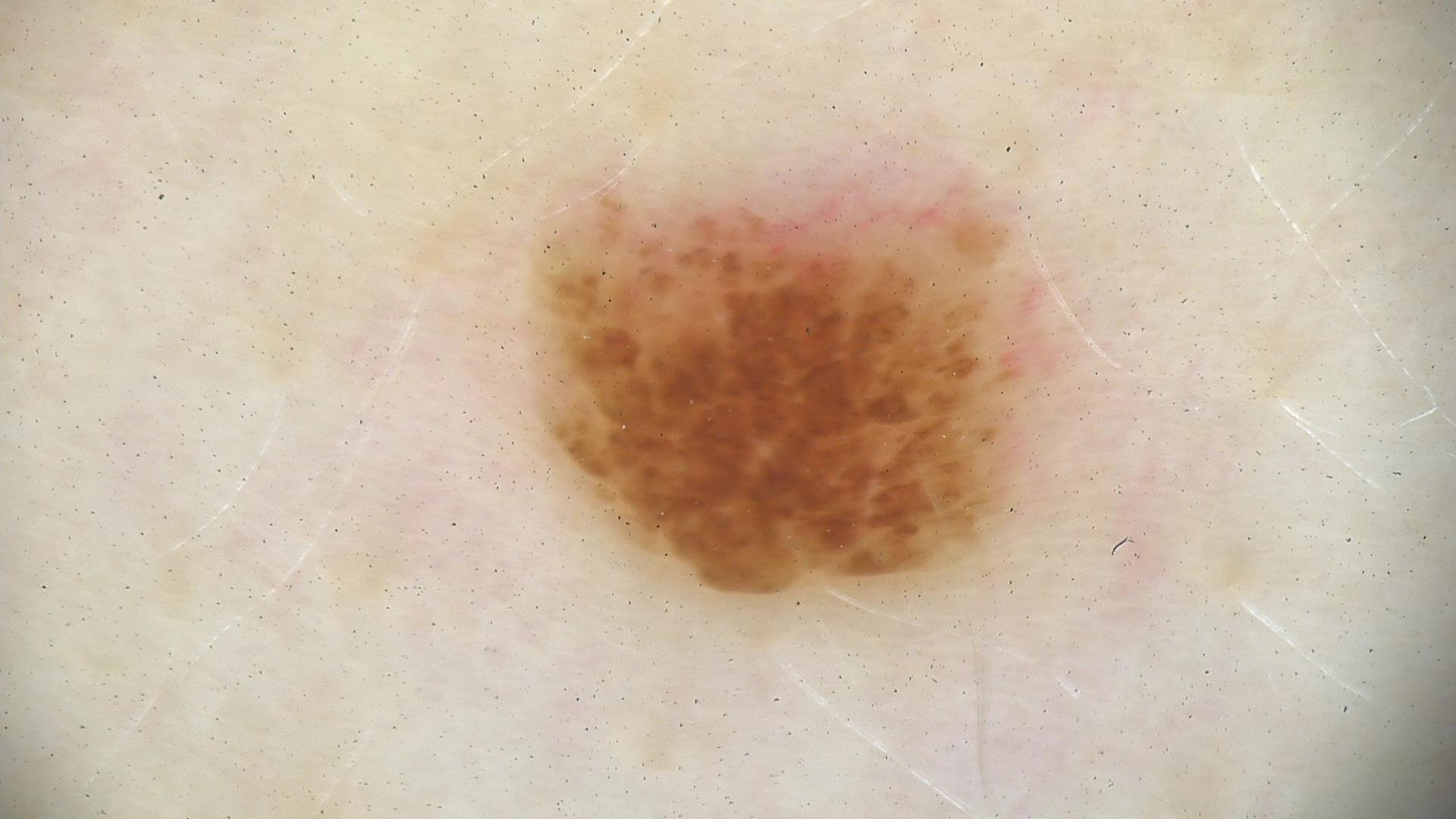Q: What is the diagnosis?
A: compound nevus (expert consensus)